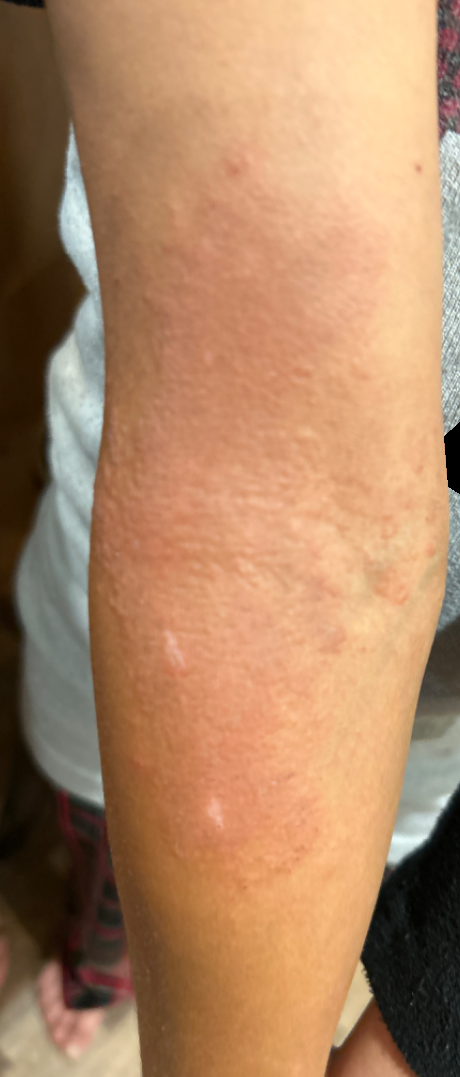Case summary:
- image framing: close-up
- affected area: arm
- clinical impression: Eczema (leading)